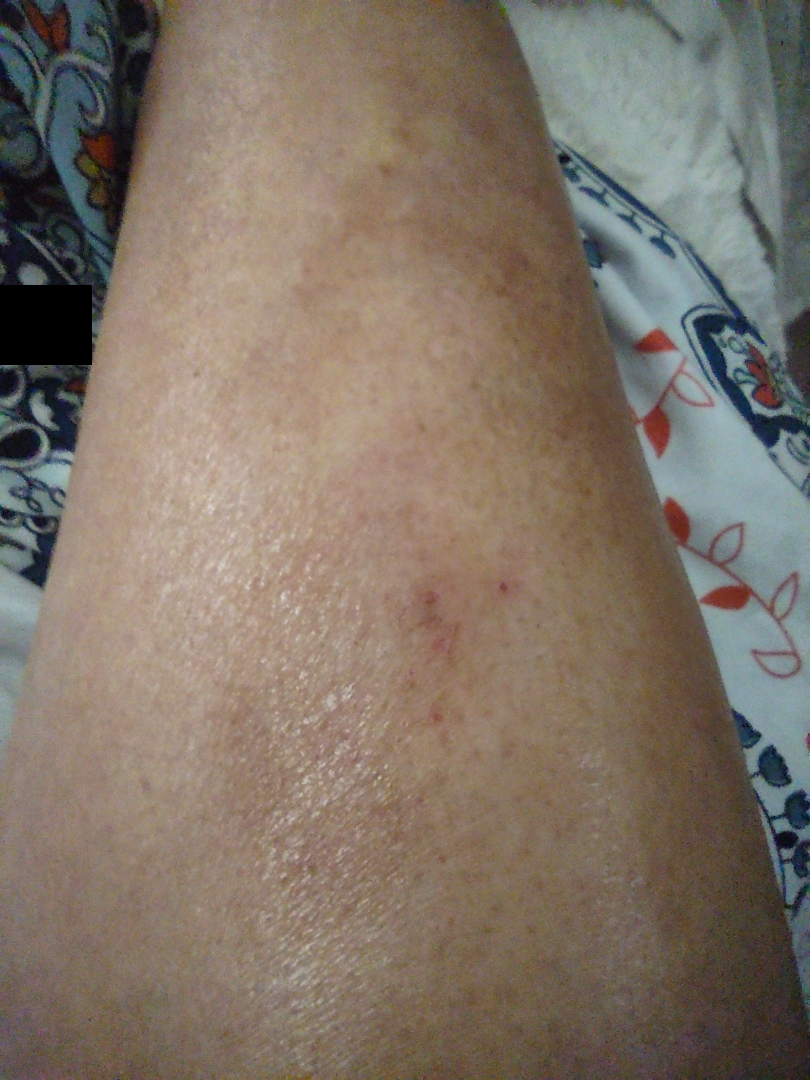Clinical context:
Reported lesion symptoms include itching, pain, bothersome appearance, darkening, enlargement and burning. A close-up photograph. The affected area is the leg. Reported duration is more than one year. The patient described the issue as a rash. The subject is female.
Assessment:
Reviewed remotely by three dermatologists: most consistent with Acute and chronic dermatitis; with consideration of Morphea/Scleroderma; possibly Stasis Dermatitis; also raised was Necrobiosis lipoidica.